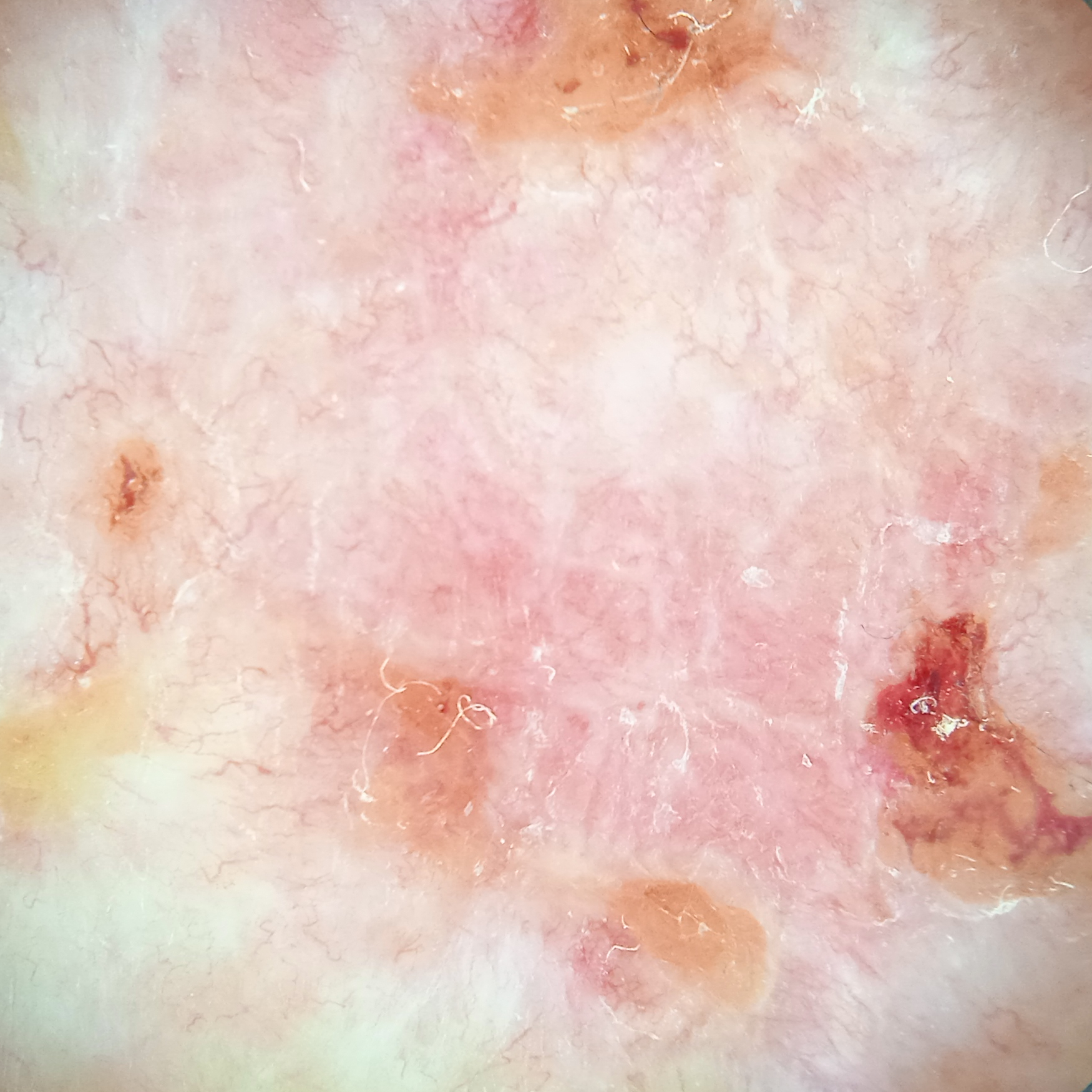Summary:
The patient says their skin reddens with sun exposure. Referred for assessment of suspected basal cell carcinoma. Few moles overall by the patient's own estimate. Located on the back. Measuring roughly 12.6 mm.
Diagnosis:
Histopathologically confirmed as a basal cell carcinoma, following excision, with tumor thickness 3 mm.